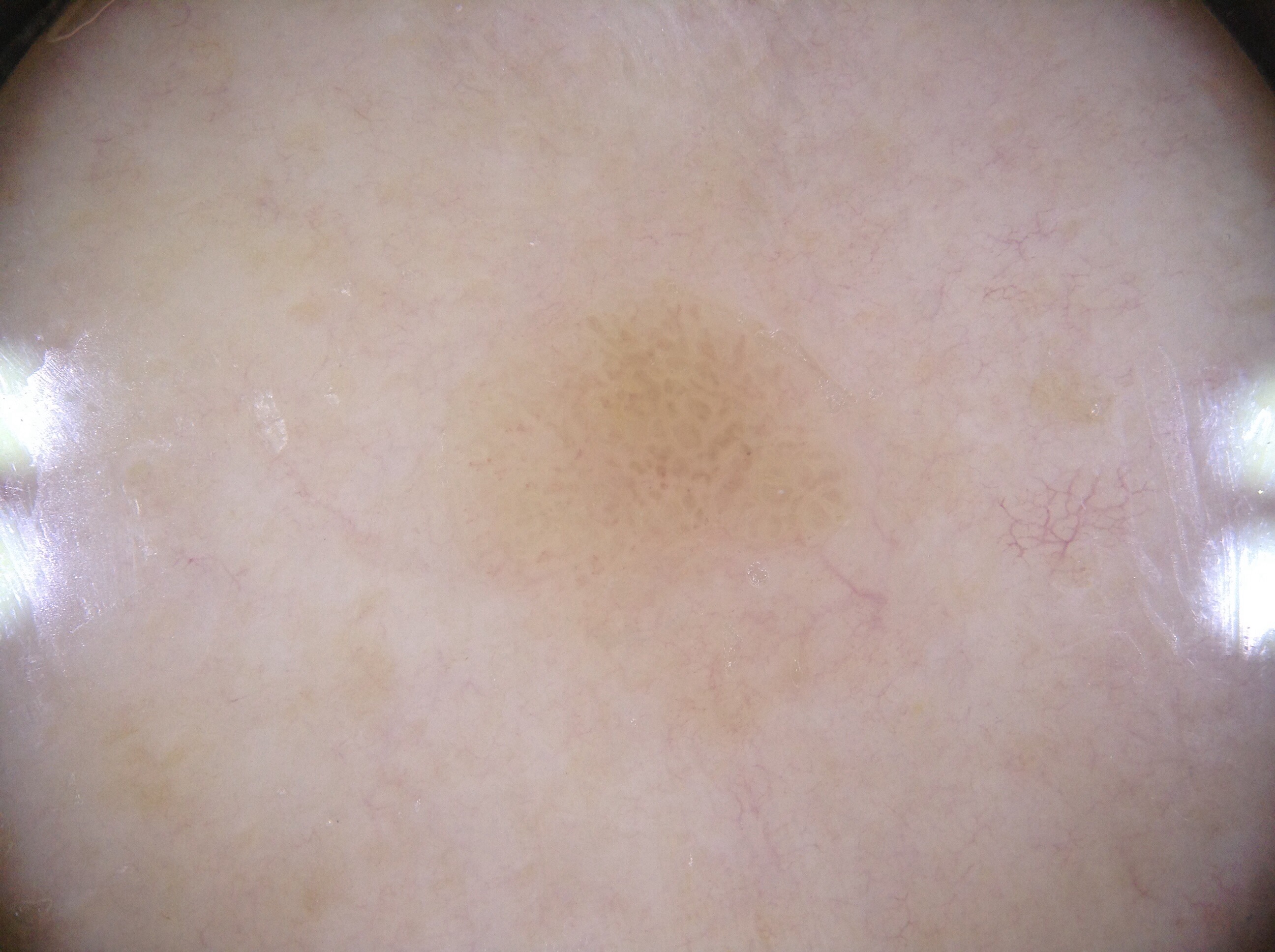Summary: The patient is a female approximately 75 years of age. Dermoscopy of a skin lesion. Dermoscopy demonstrates no streaks, milia-like cysts, pigment network, or negative network. The lesion is bounded by <bbox>529, 305, 827, 572</bbox>. Impression: The lesion was assessed as a seborrheic keratosis, a benign skin lesion.